The lesion involves the arm; the photograph was taken at a distance.
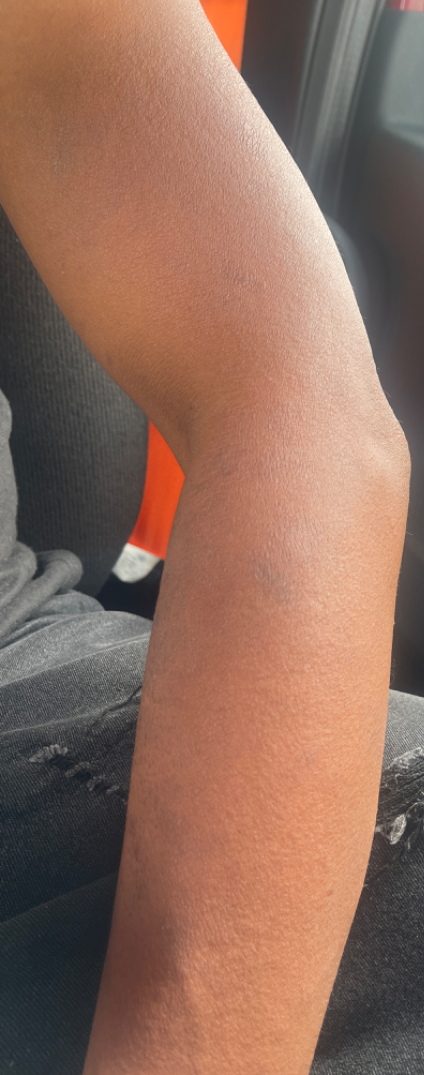Q: What was the assessment?
A: indeterminate from the photograph
Q: Patient's own categorization?
A: a rash
Q: When did this start?
A: one to four weeks
Q: Texture?
A: rough or flaky and raised or bumpy
Q: Reported symptoms?
A: itching and darkening